This is a close-up image. Female patient, age 18–29. Located on the top or side of the foot, back of the hand, palm and sole of the foot: 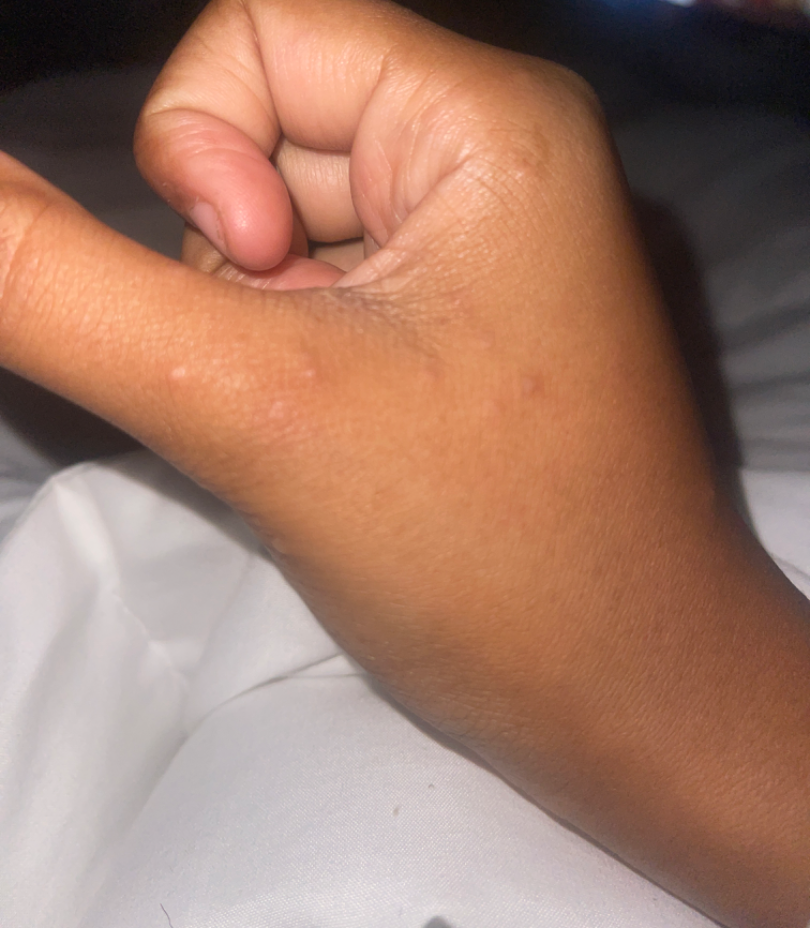Case summary:
- symptoms: burning and itching
- present for: one to four weeks
- skin tone: Fitzpatrick phototype V
- self-categorized as: a rash
- impression: the leading consideration is Scabies; possibly Eczema; less probable is Molluscum Contagiosum; less likely is Allergic Contact Dermatitis; lower on the differential is Hypersensitivity